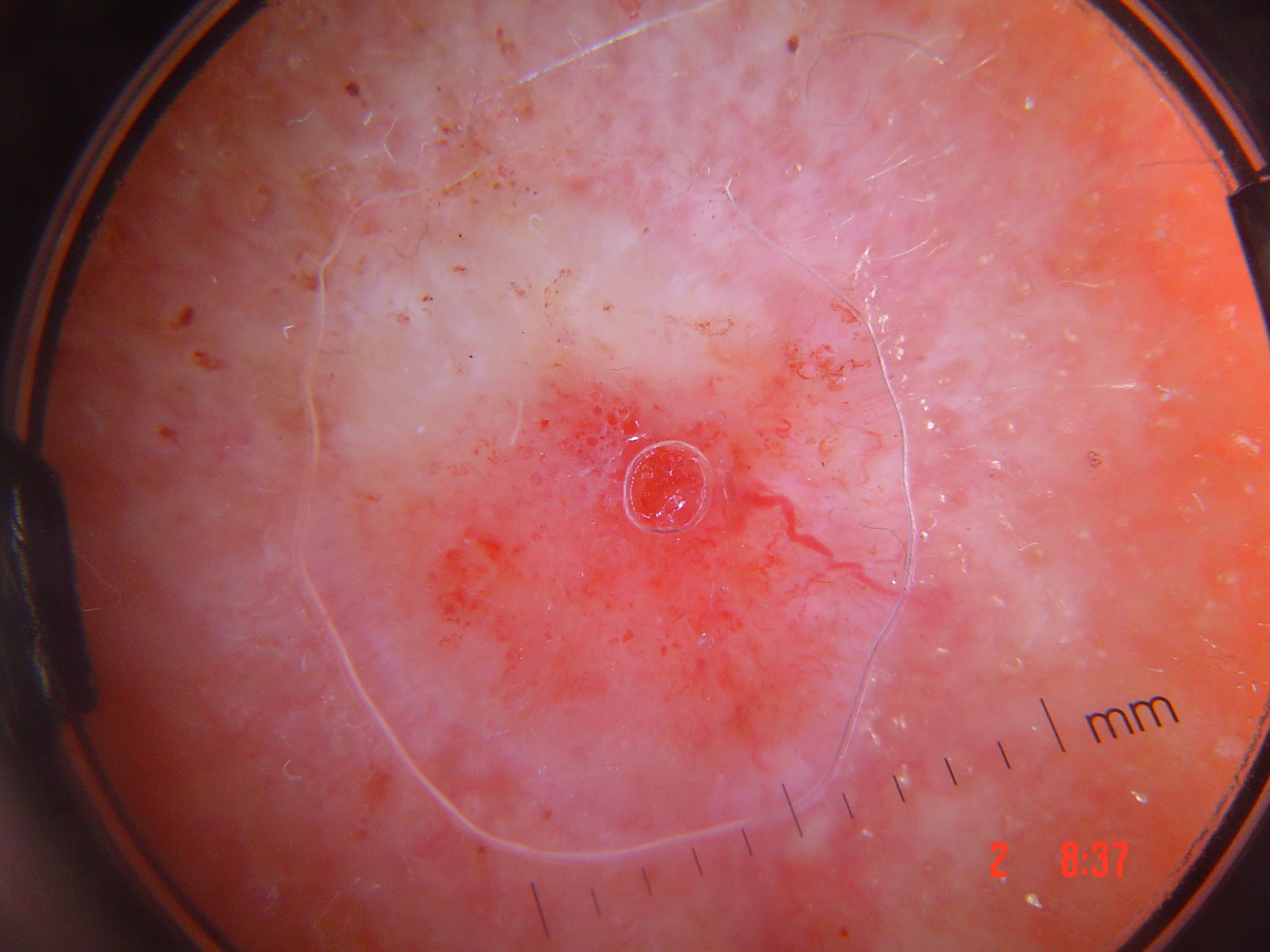The morphology is that of a keratinocytic lesion. Histopathology confirmed a squamous cell carcinoma.